This is a dermoscopic photograph of a skin lesion · a female patient, approximately 60 years of age.
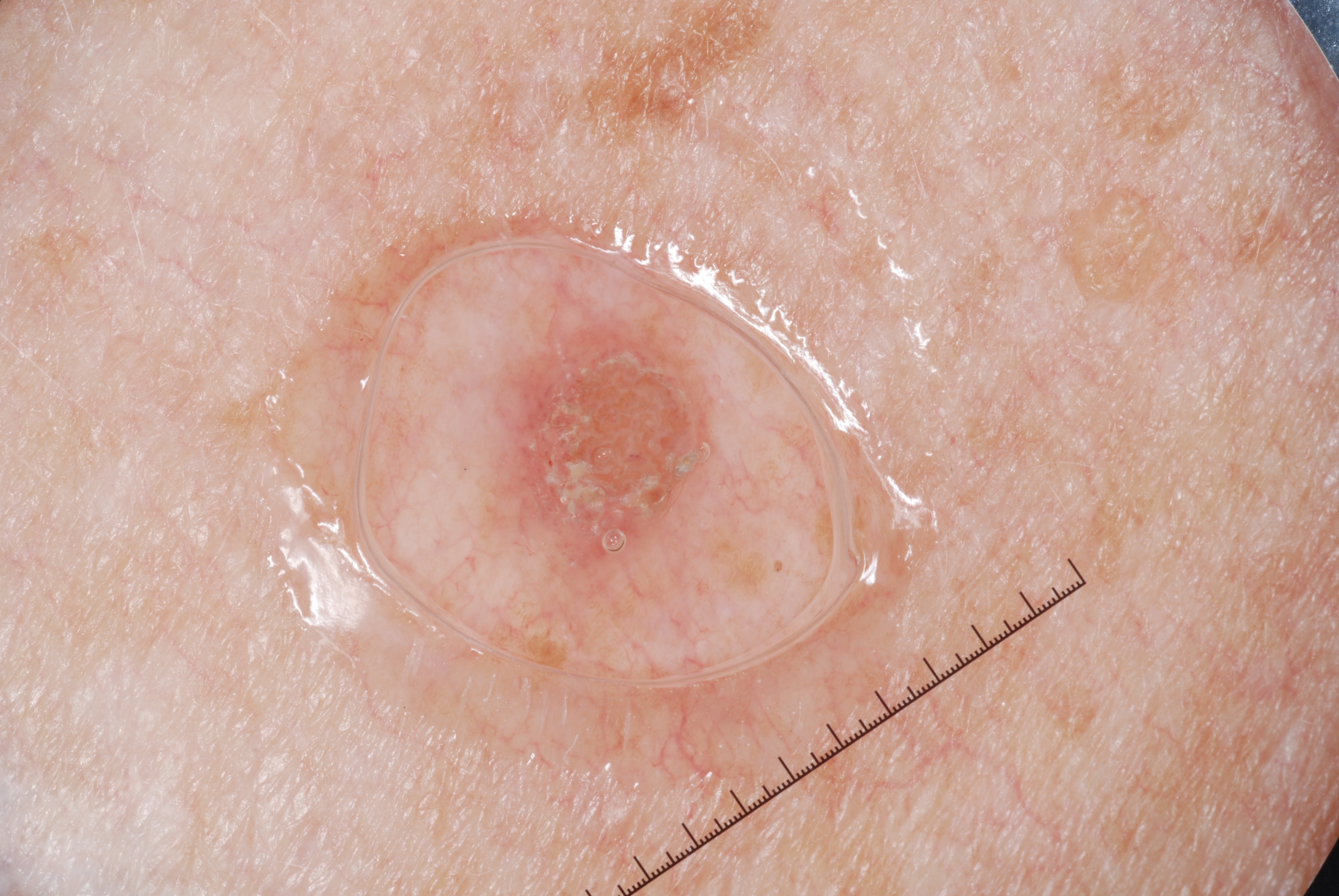Findings: As (left, top, right, bottom), the lesion's extent is 484/279/717/609. The lesion occupies roughly 4% of the field. Dermoscopically, the lesion shows milia-like cysts, with no negative network, streaks, or pigment network. Impression: The diagnostic assessment was a seborrheic keratosis.